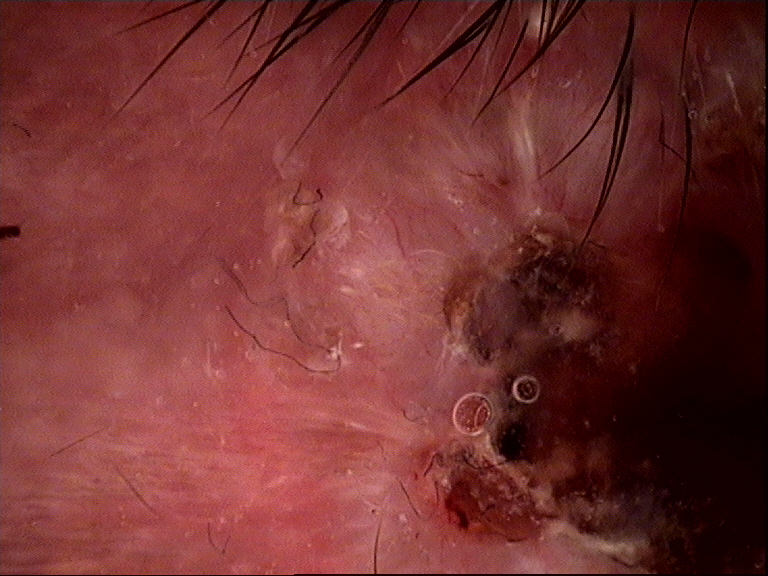modality = dermoscopy; classification = keratinocytic; pathology = basal cell carcinoma (biopsy-proven).